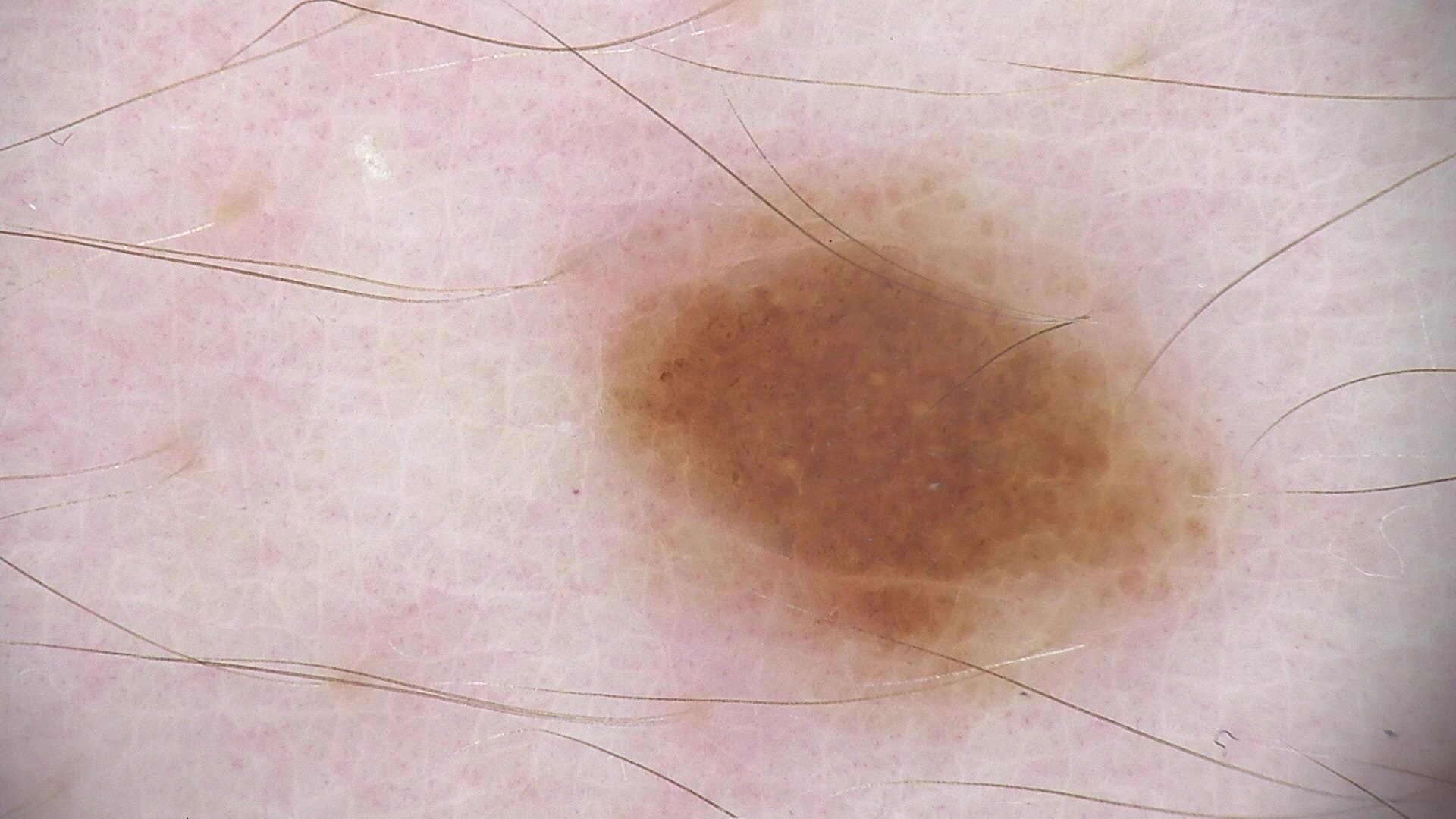imaging: dermatoscopy
diagnosis: dysplastic junctional nevus (expert consensus)